A skin lesion imaged with a dermatoscope:
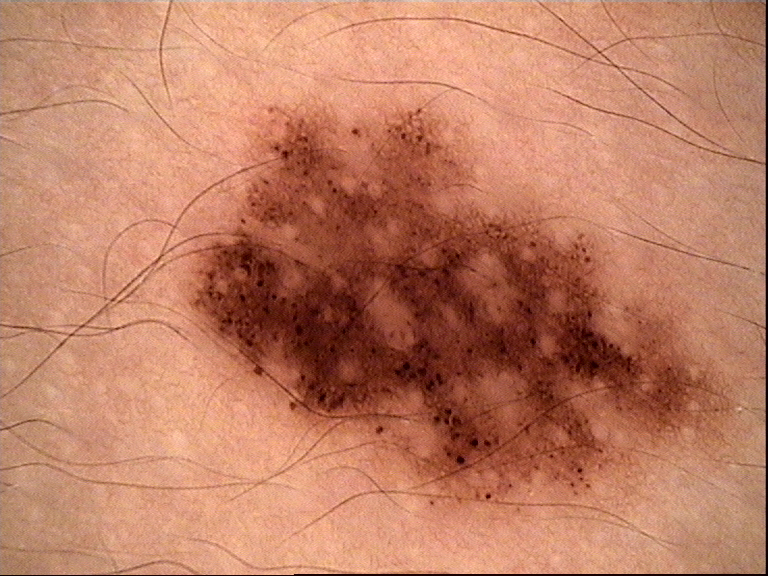Conclusion: Labeled as a dysplastic junctional nevus.